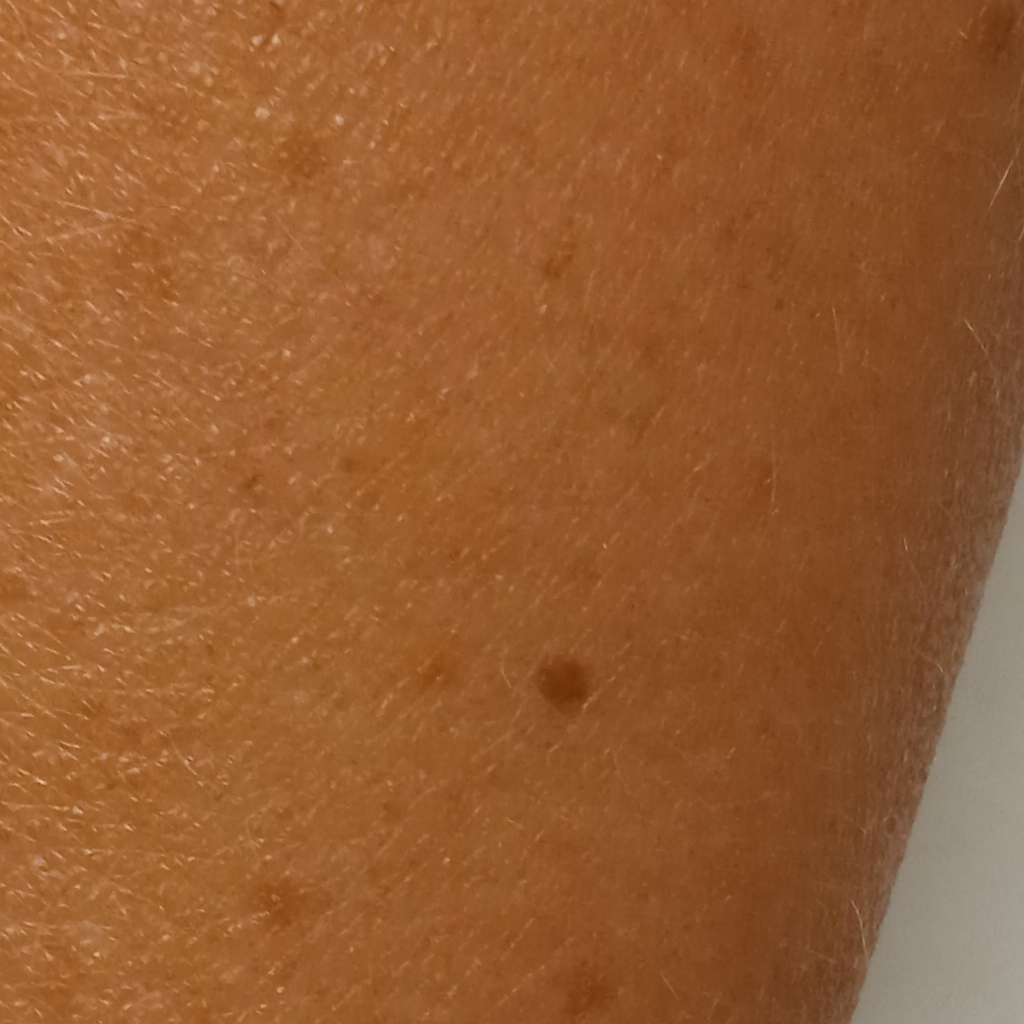Imaged for a research study, with no referral diagnosis recorded. A female subject aged 47. The patient says their skin tans without first burning. A clinical photograph showing a skin lesion. On a questionnaire the patient reported a history of sunbed use. Located on the back. The lesion measures approximately 1.8 mm. The diagnostic impression was a melanocytic nevus.